A dermoscopic photograph of a skin lesion.
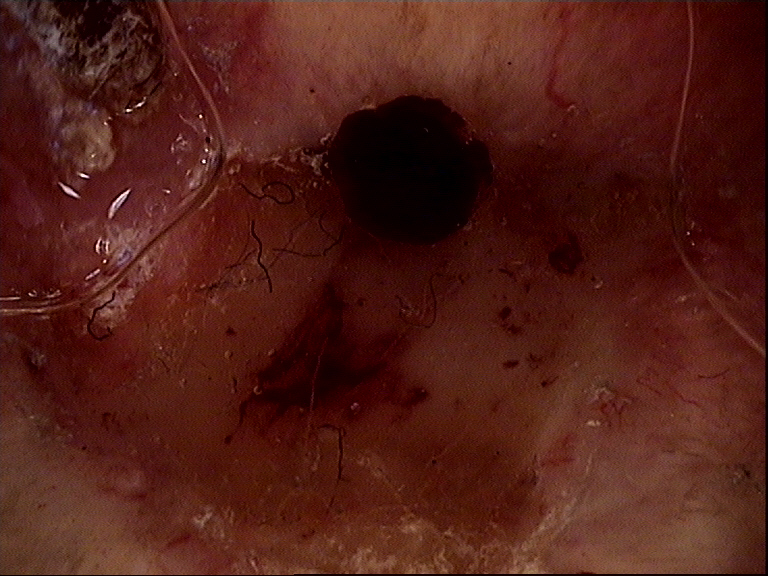label = squamous cell carcinoma (biopsy-proven).